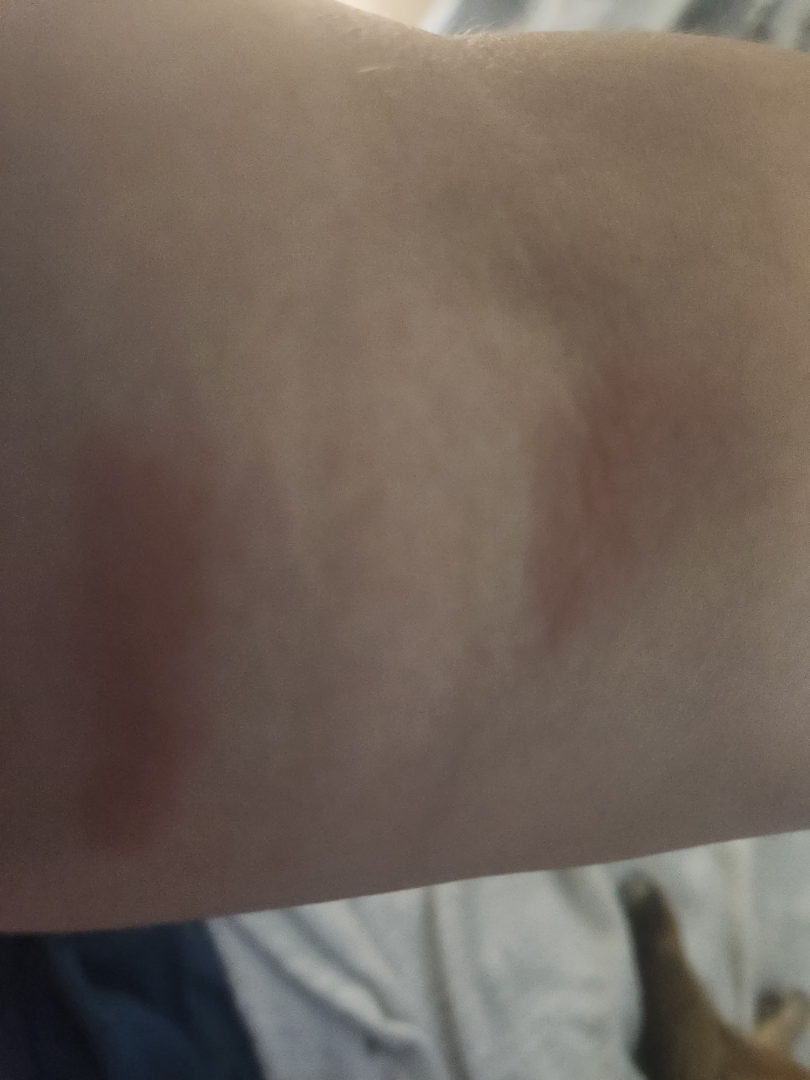differential:
  tied_lead:
    - Urticaria
    - Burn of skin
    - Allergic Contact Dermatitis